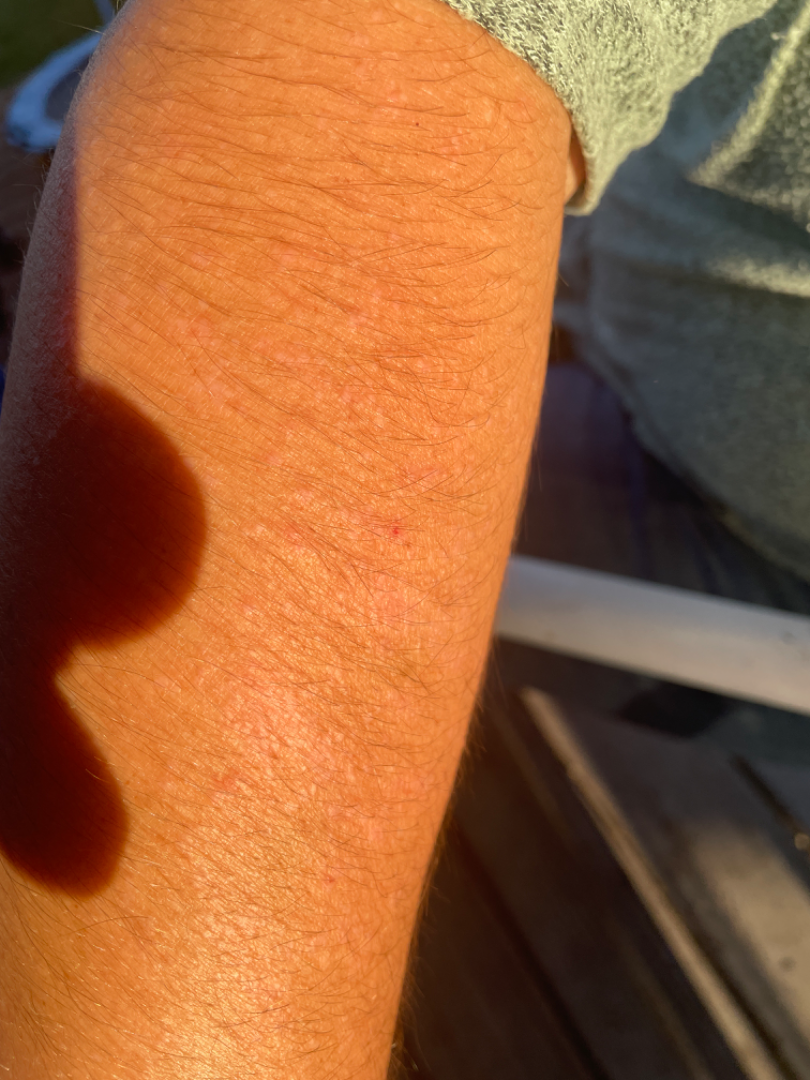assessment: ungradable on photographic review.